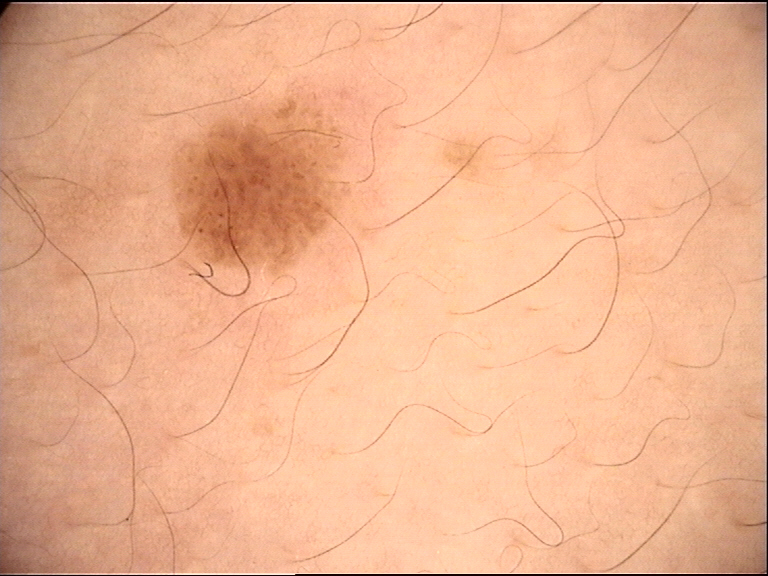Conclusion:
Labeled as a seborrheic keratosis.